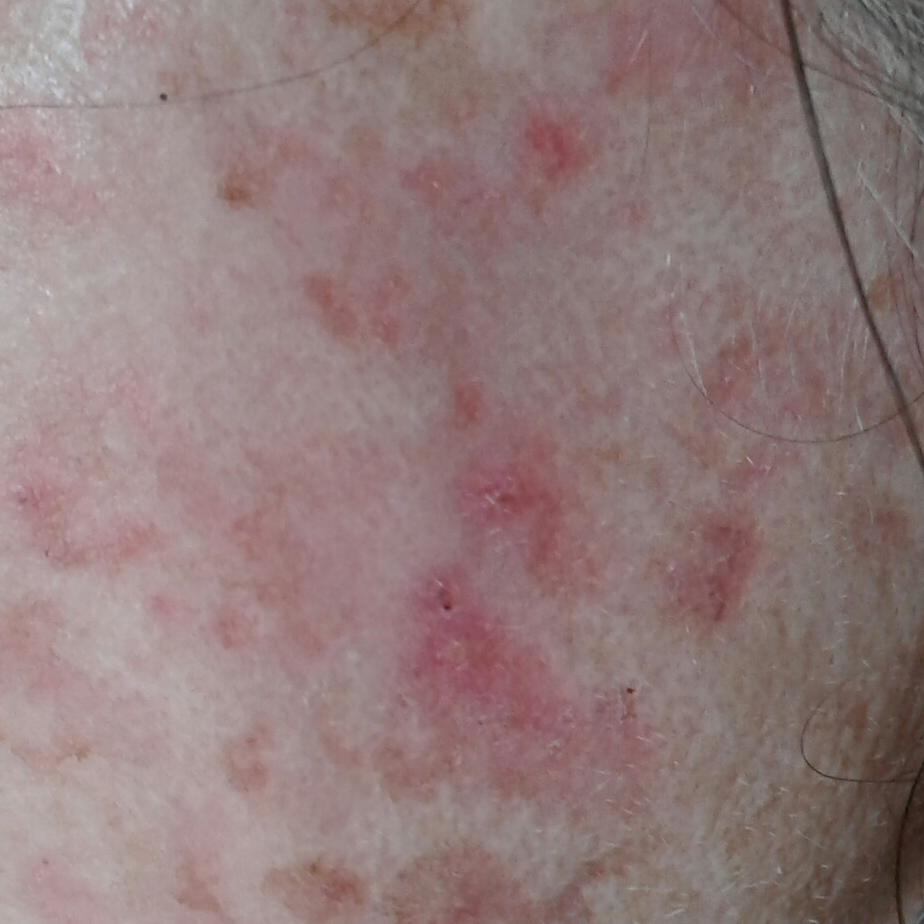A clinical photo of a skin lesion taken with a smartphone.
A subject 75 years of age.
Located on the face.
The diagnostic impression was an actinic keratosis.